The lesion involves the arm. An image taken at an angle. Male contributor, age 18–29:
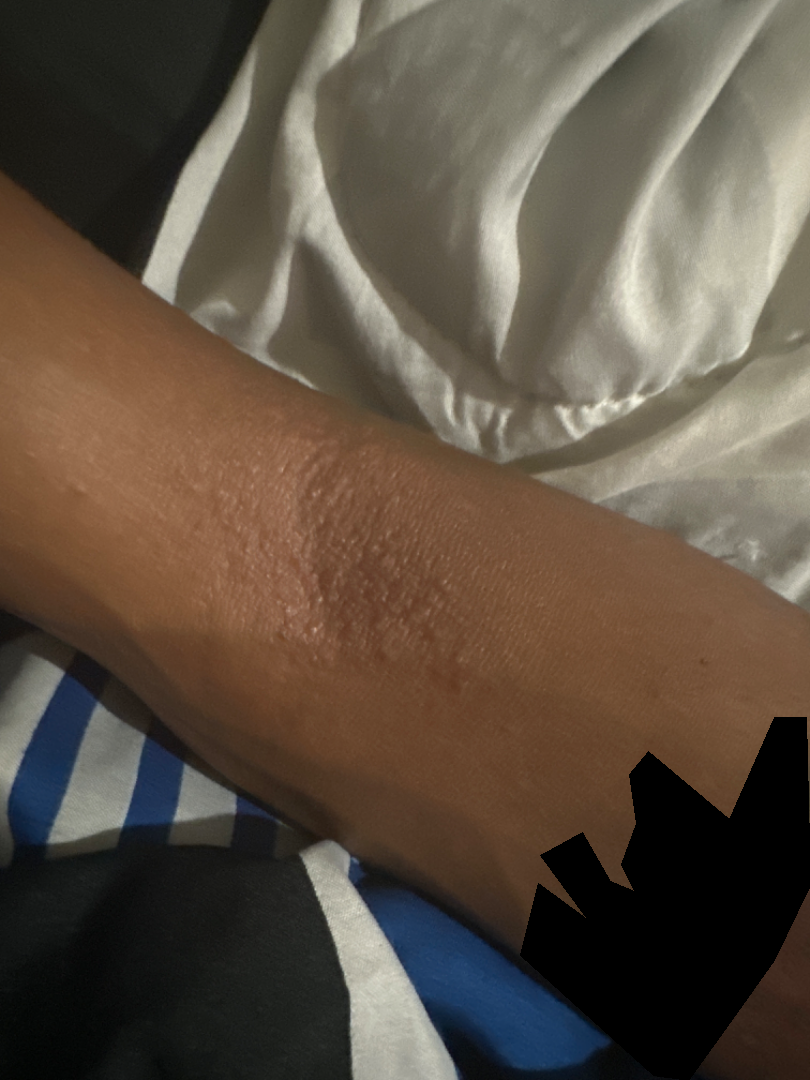On remote dermatologist review, consistent with Eczema.